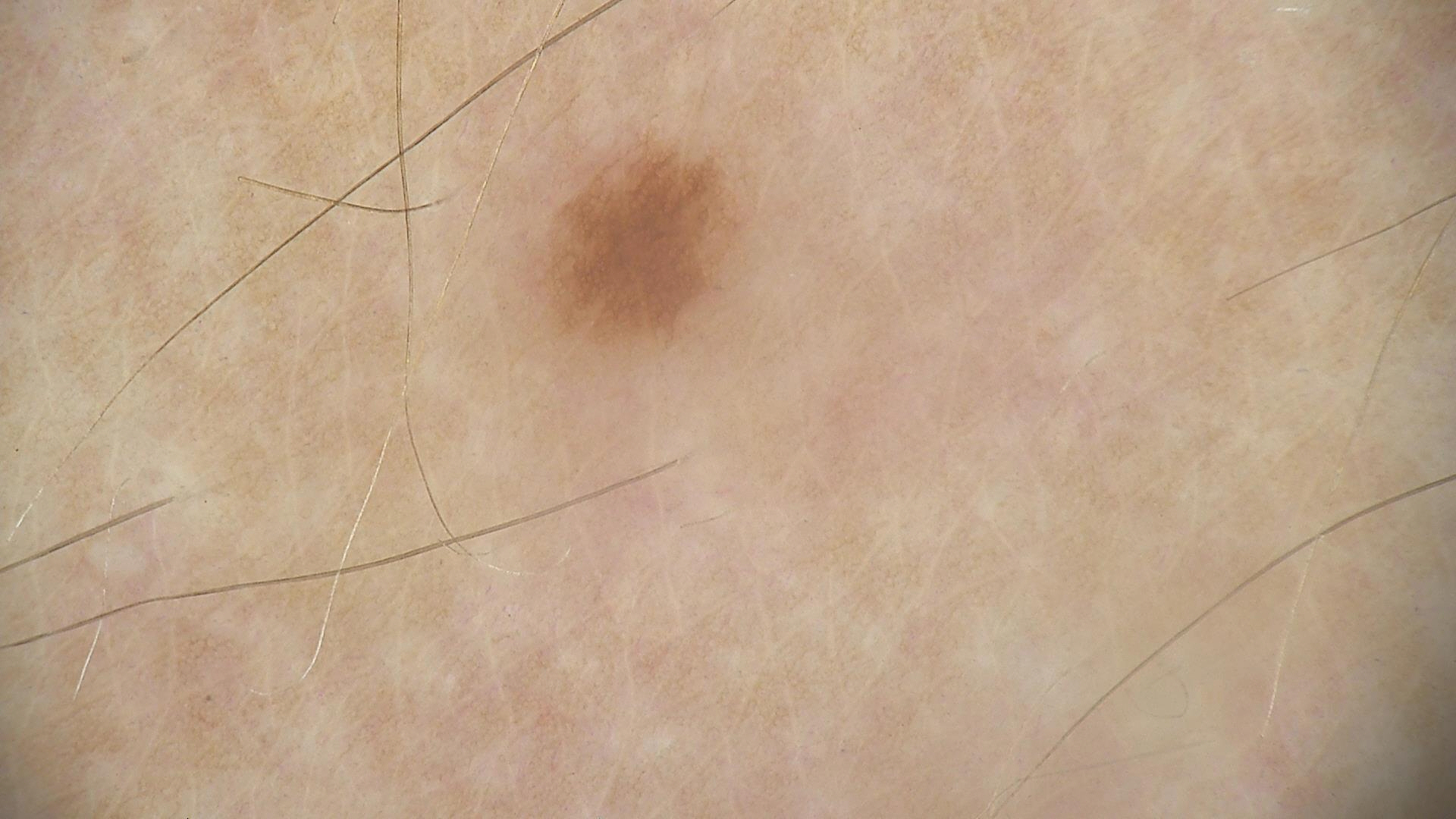image type: dermatoscopy
diagnosis: dysplastic junctional nevus (expert consensus)